A skin lesion imaged with a dermatoscope. The patient says their skin tans without first burning. A male patient 54 years of age. A moderate number of moles by the patient's own estimate. Imaged for a research study, with no referral diagnosis recorded — 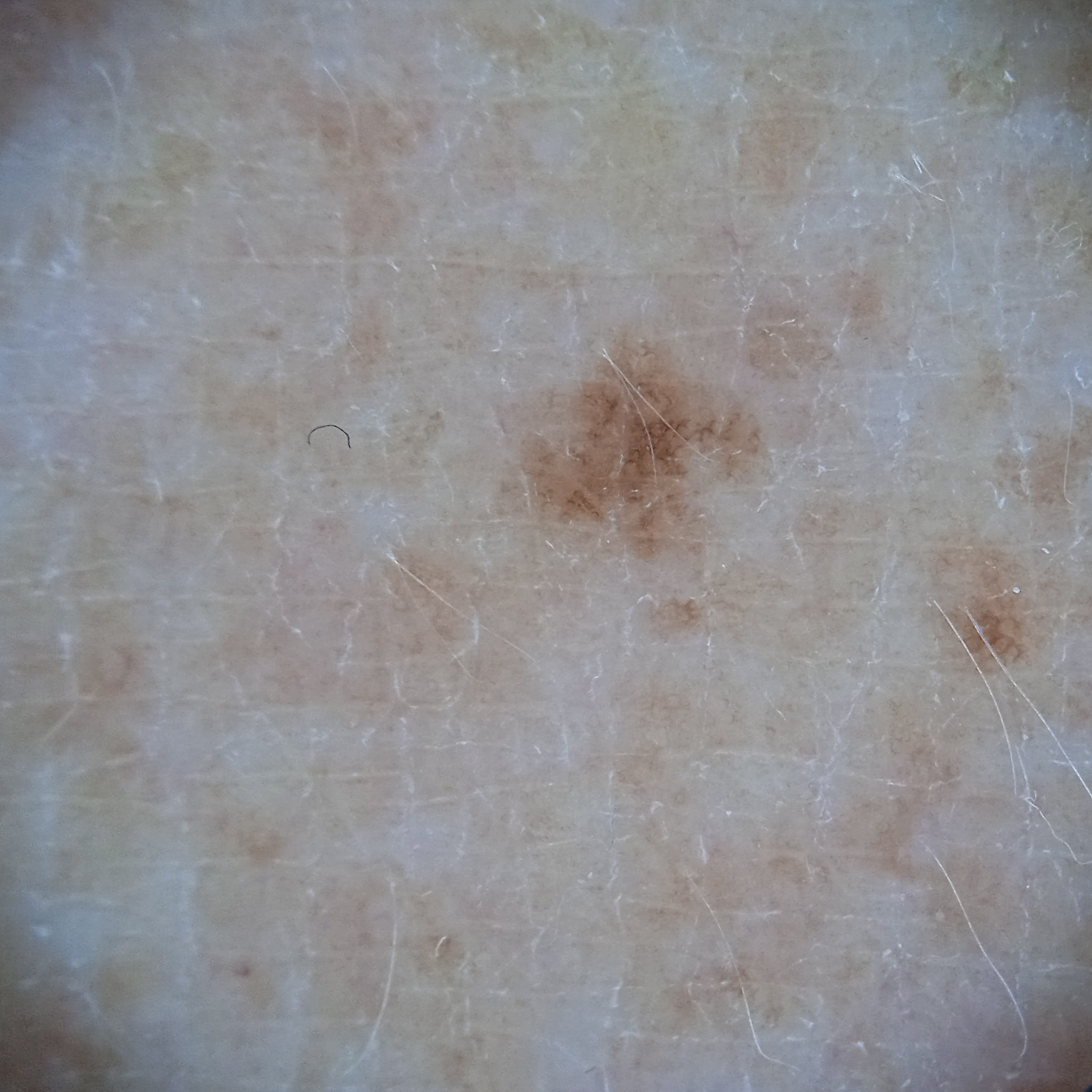Located on an arm. The lesion is about 2.6 mm across. The four-dermatologist consensus diagnosis was a melanocytic nevus; the reviewers were moderately confident; an alternative consideration was a lentigo and a solar lentigo.